The patient reports a personal history of cancer; a female patient 84 years old — 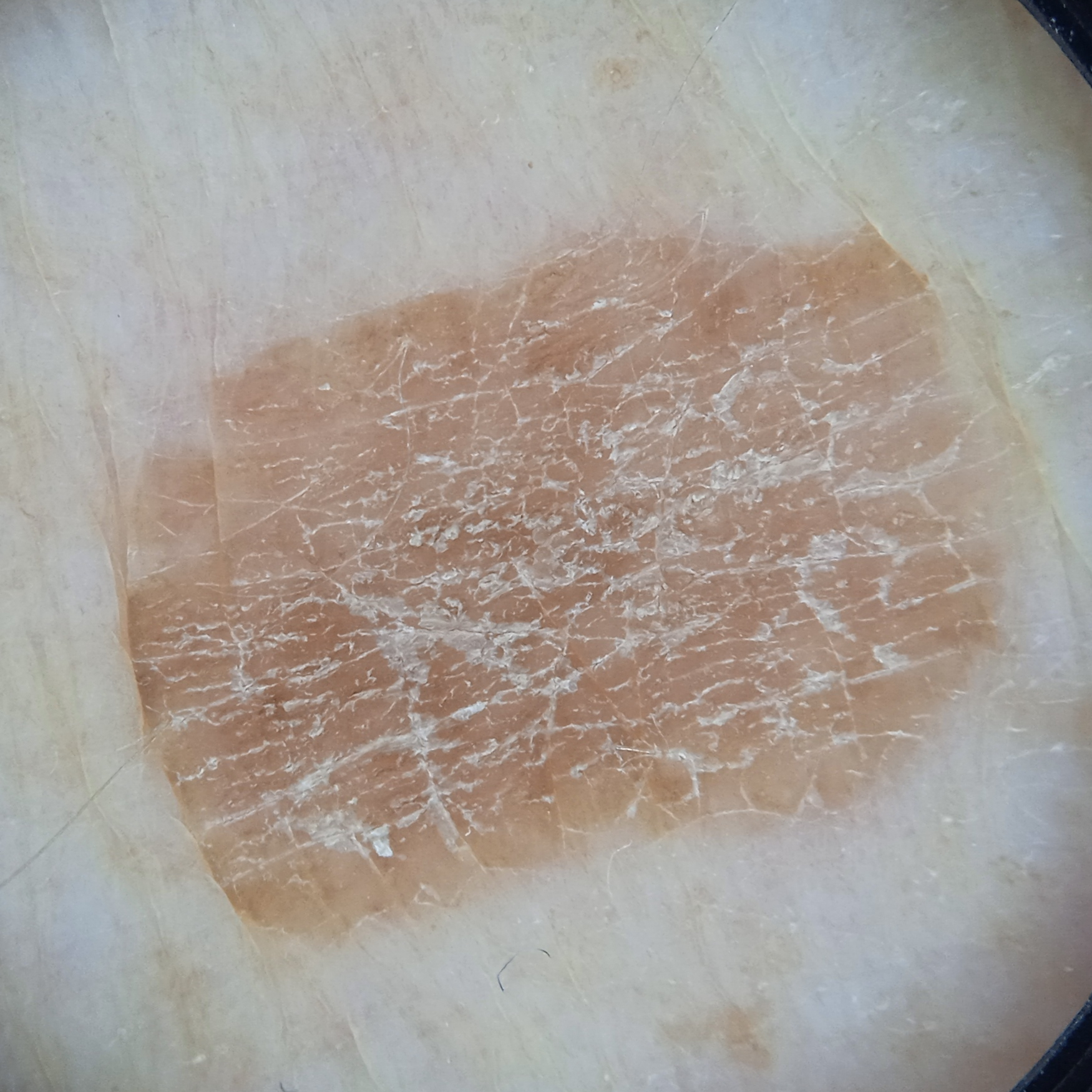The lesion measures approximately 11.2 mm. The consensus diagnosis for this lesion was a seborrheic keratosis.